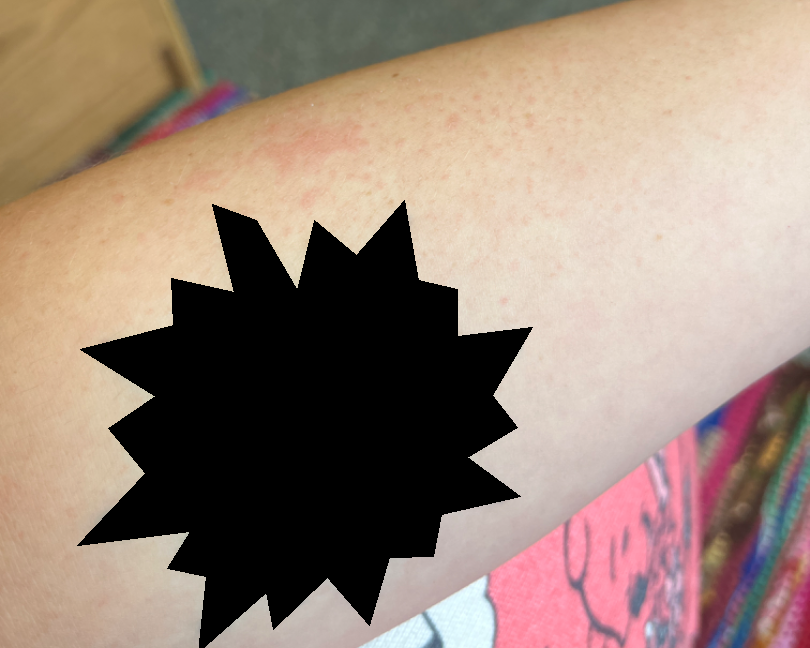Notes:
- assessment — not assessable
- patient-reported symptoms — bothersome appearance and itching
- self-categorized as — skin that appeared healthy to them
- skin tone — Fitzpatrick III; lay graders estimated MST 2 or 3
- photo taken — at an angle
- present for — about one day
- site — arm
- texture — raised or bumpy